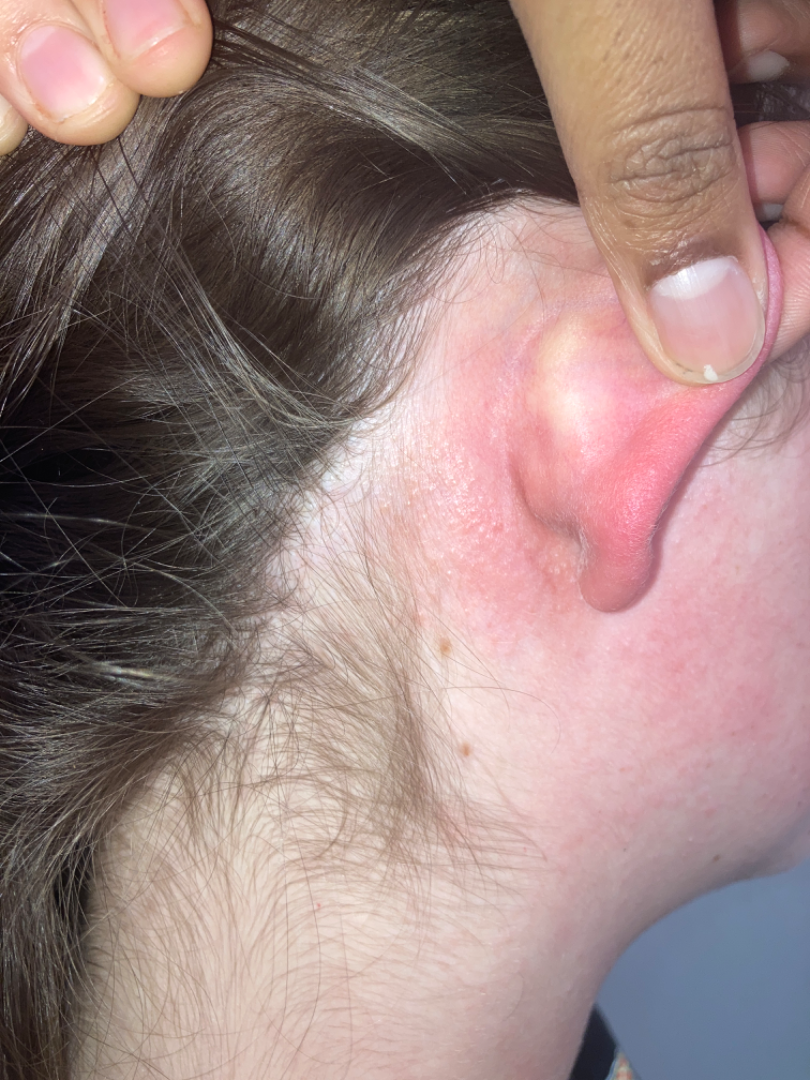On teledermatology review: the favored diagnosis is Seborrheic Dermatitis; also consider Eczema.